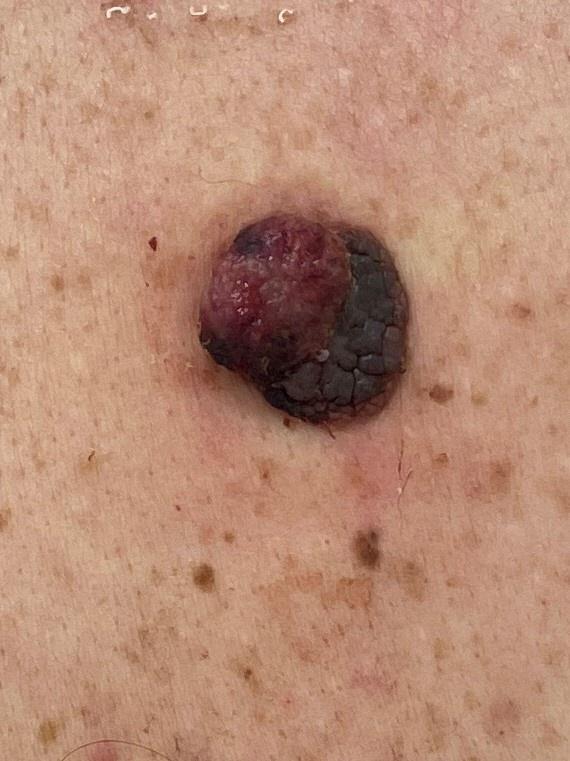<skin_lesion>
<image>clinical photo (overview)</image>
<patient>
<age_approx>55</age_approx>
<sex>male</sex>
</patient>
<diagnosis>
<name>Melanoma</name>
<malignancy>malignant</malignancy>
<confirmation>histopathology</confirmation>
</diagnosis>
</skin_lesion>